The chart records tobacco use. Fitzpatrick skin type II. A clinical photograph showing a skin lesion. A female subject in their 70s: 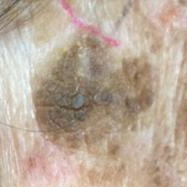size: 18 × 15 mm
symptoms: elevation, growth / no pain
diagnostic label: seborrheic keratosis (clinical consensus)